Close-up view, the affected area is the top or side of the foot and leg: 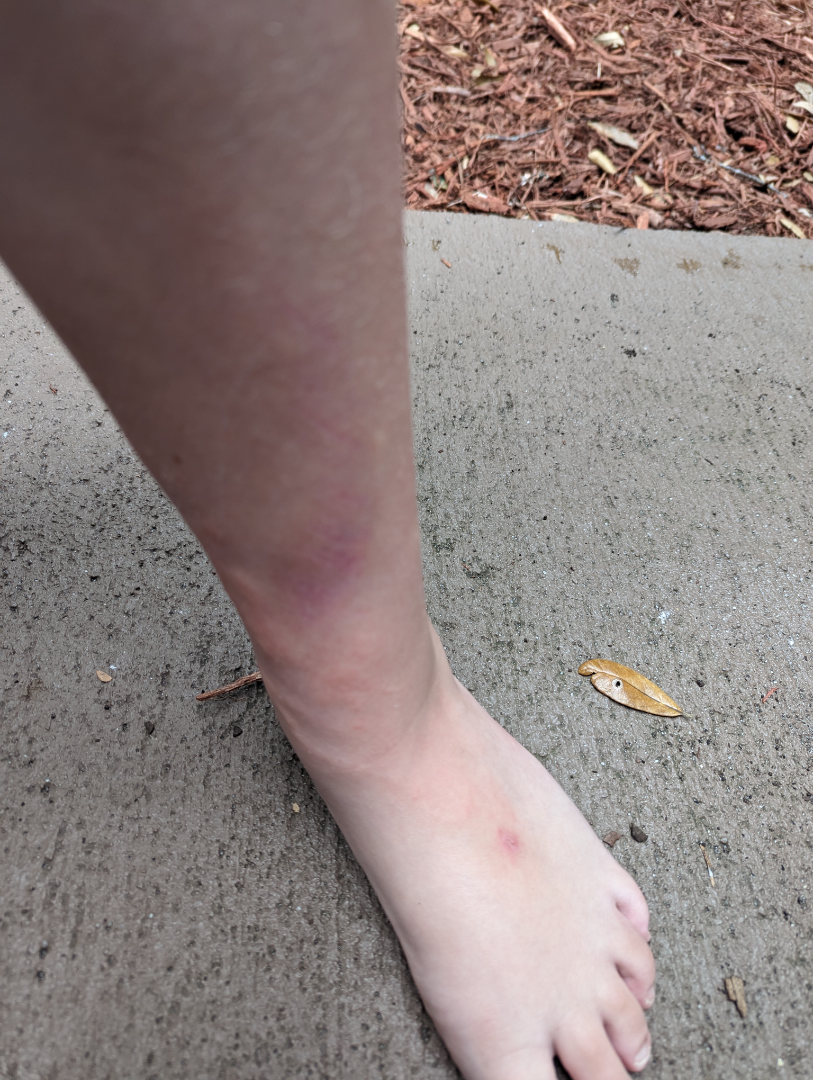The case was indeterminate on photographic review.